The lesion involves the arm · the subject is 70–79, female · the photograph is a close-up of the affected area: 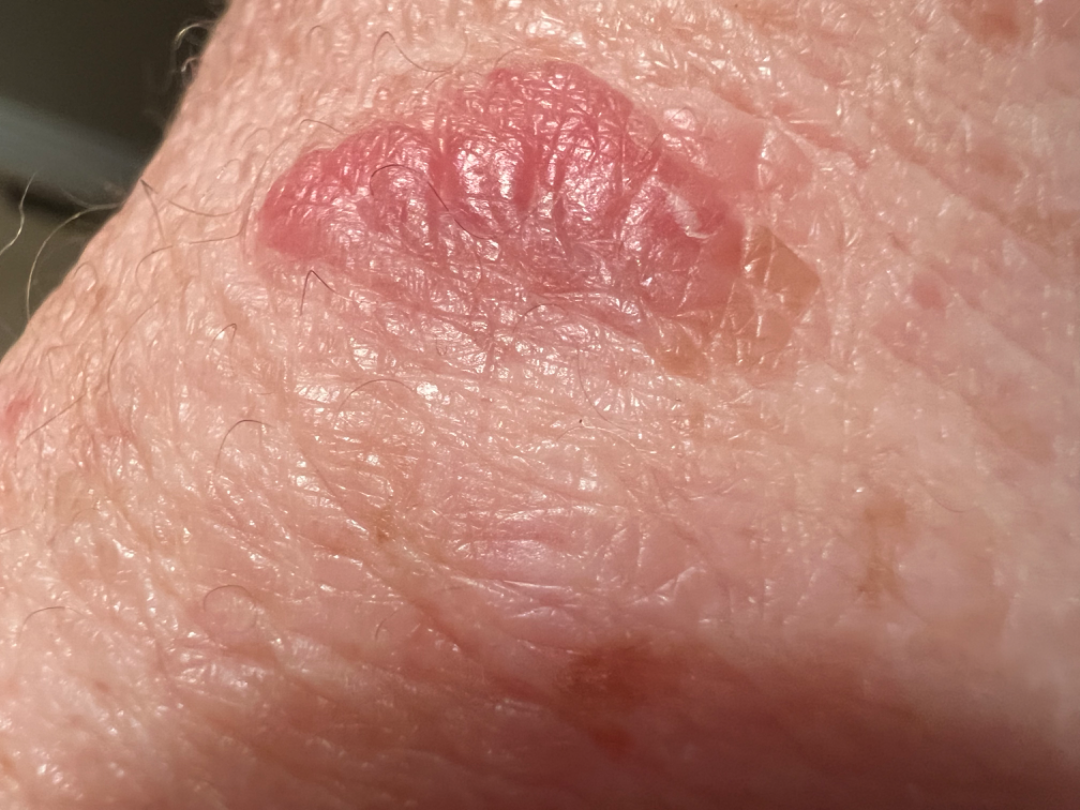Review: The reviewing dermatologist was unable to assign a differential diagnosis from the image. Patient information: Reported duration is one to three months. The contributor notes the lesion is raised or bumpy. No relevant lesion symptoms reported. Skin tone: Fitzpatrick phototype II.